A male subject in their early 60s. A clinical close-up photograph of a skin lesion.
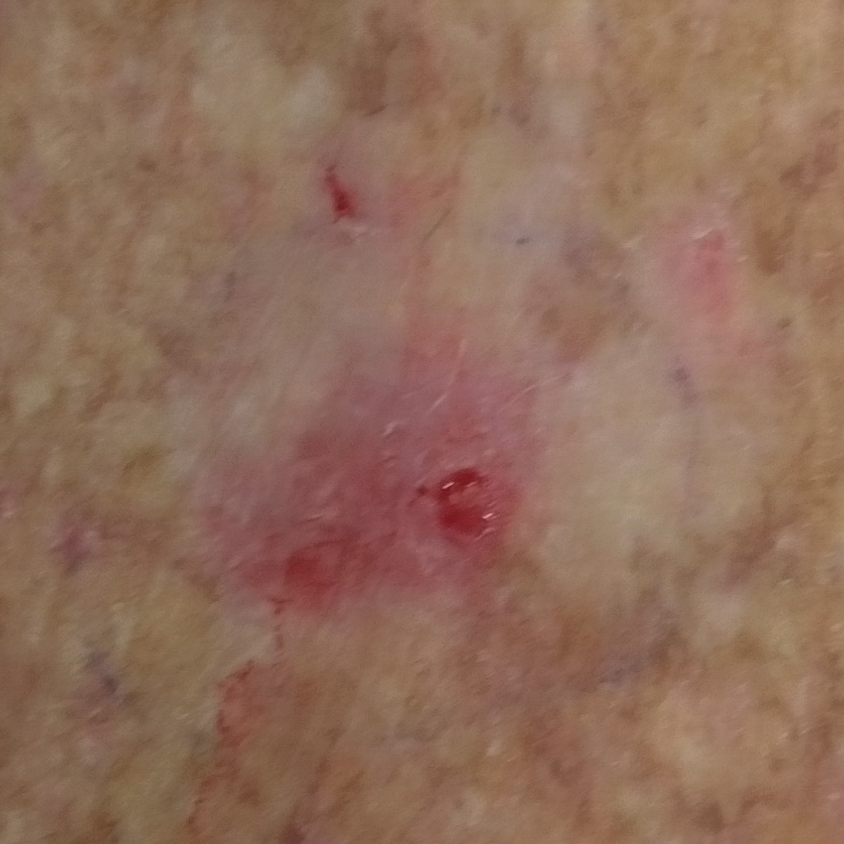Diagnosis:
Histopathologically confirmed as a basal cell carcinoma.